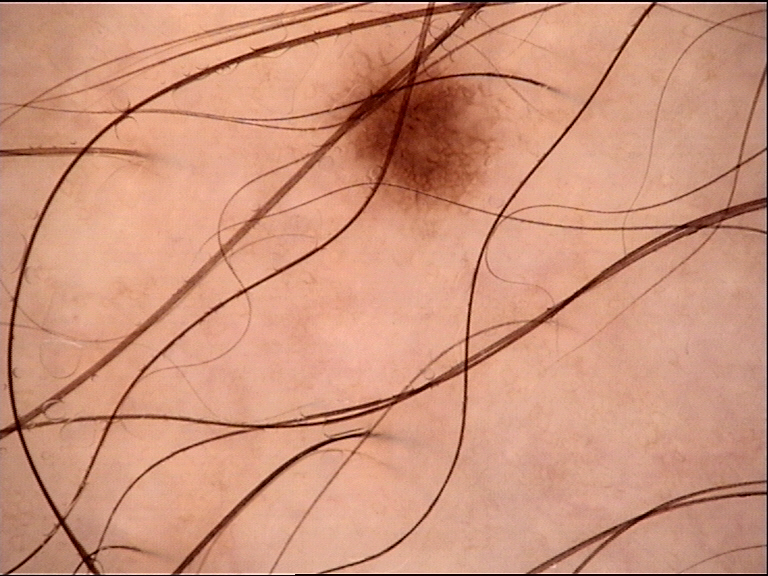A dermoscopic photograph of a skin lesion. The diagnostic label was a benign lesion — a dysplastic junctional nevus.